The patient notes the condition has been present for less than one week. Texture is reported as raised or bumpy. The lesion involves the arm. Close-up view. The patient considered this a rash:
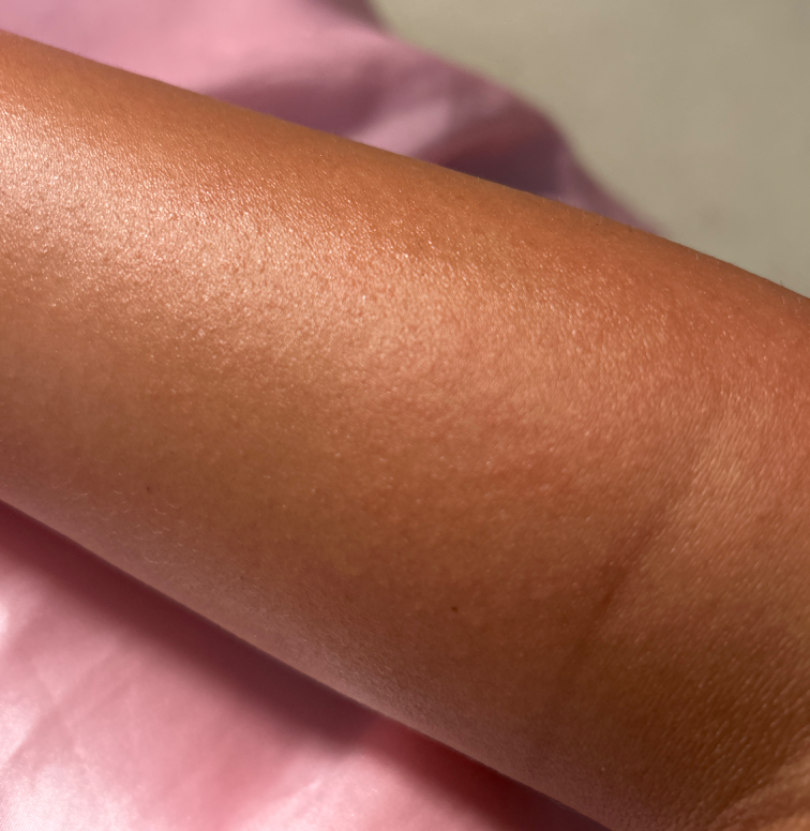assessment: ungradable on photographic review.